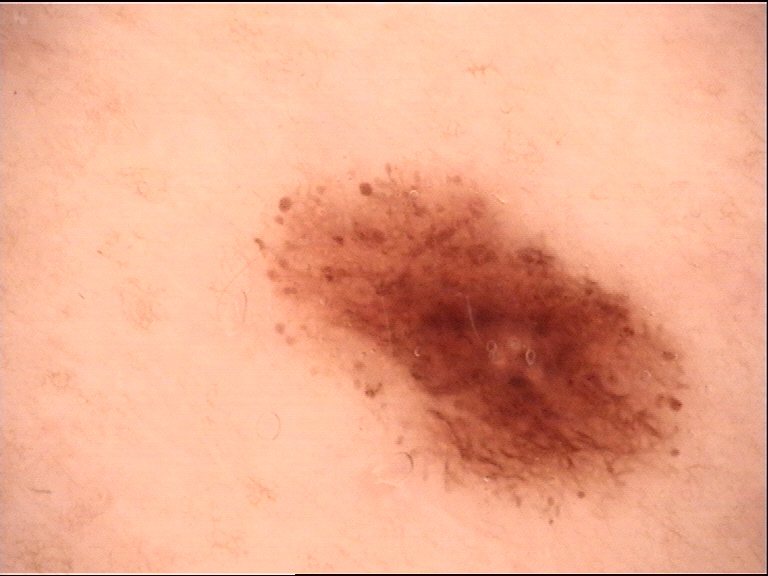Case:
• image type: dermoscopy
• diagnostic label: dysplastic junctional nevus (expert consensus)